The affected area is the palm, back of the hand, arm and top or side of the foot. The contributor is 40–49, female. This is a close-up image — 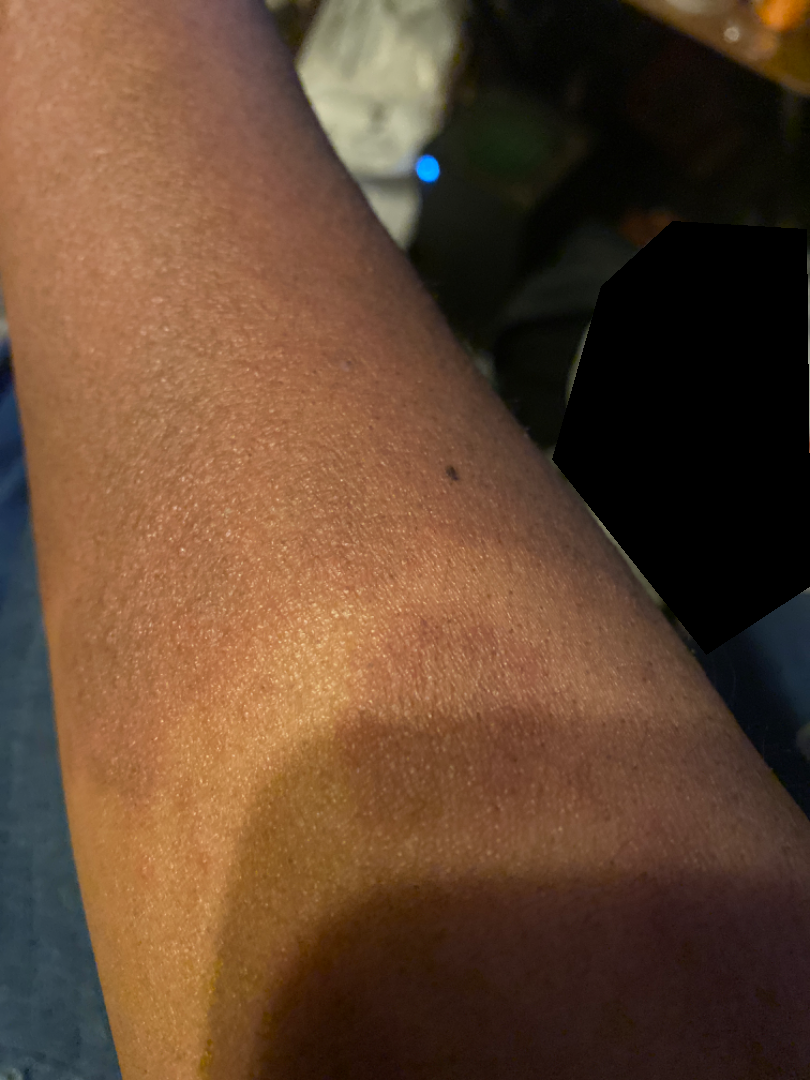Q: Patient's own categorization?
A: a rash
Q: Constitutional symptoms?
A: none reported
Q: Texture?
A: rough or flaky
Q: How long has this been present?
A: one to three months
Q: What symptoms does the patient report?
A: darkening, itching, enlargement, burning and bleeding
Q: What is the dermatologist's impression?
A: most consistent with Acute and chronic dermatitis